The photo was captured at a distance; the arm and head or neck are involved.
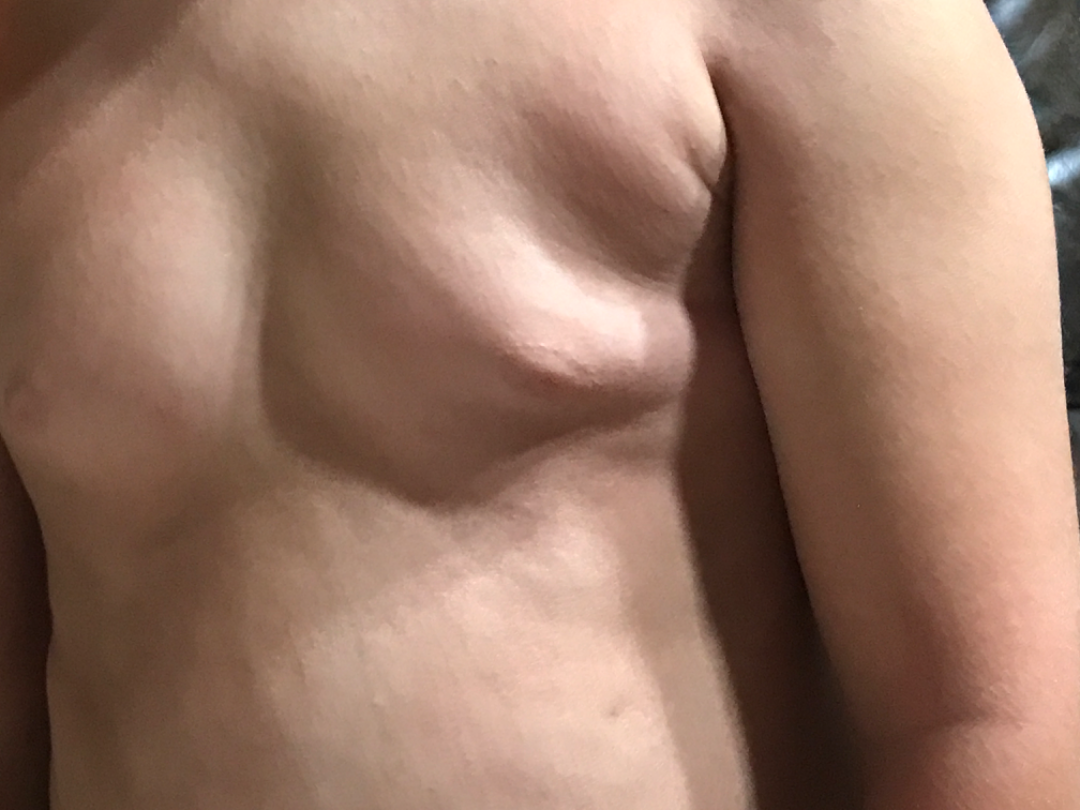impression = Miliaria and Folliculitis were considered with similar weight.